Located on the arm; the photograph was taken at a distance; texture is reported as fluid-filled, rough or flaky and raised or bumpy; the contributor is a female aged 30–39.
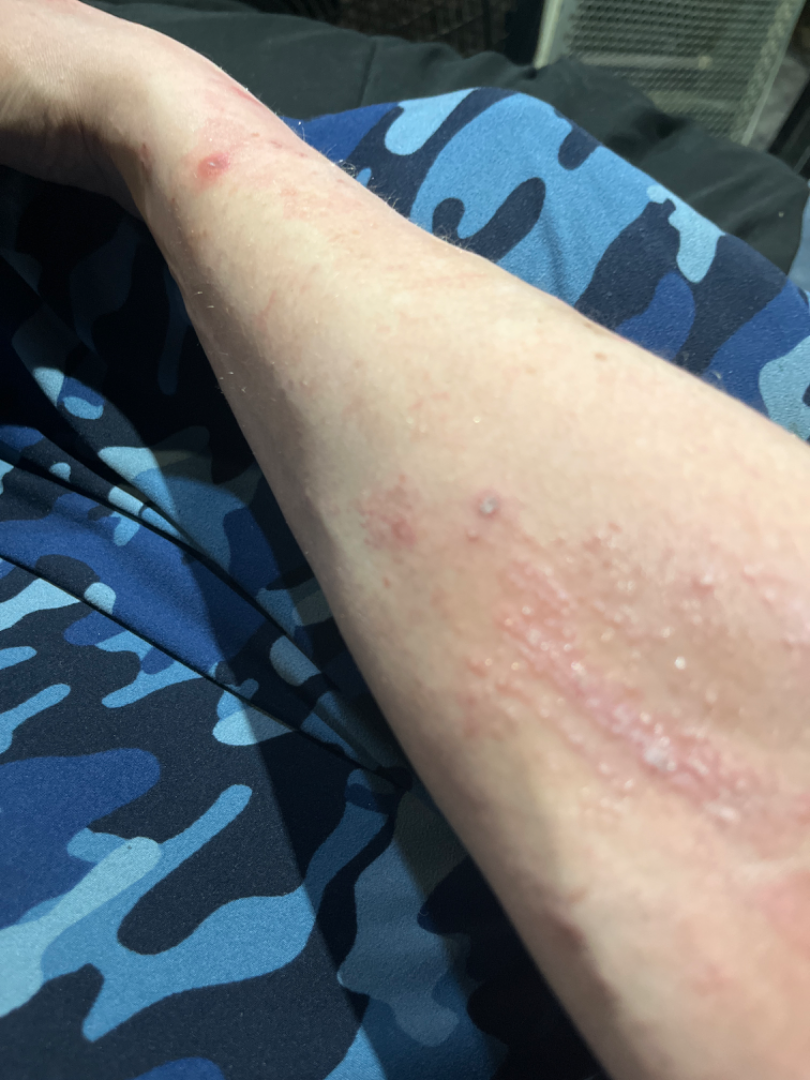Review: On remote dermatologist review: Psoriasis, Eczema and Lichen Simplex Chronicus were considered with similar weight.